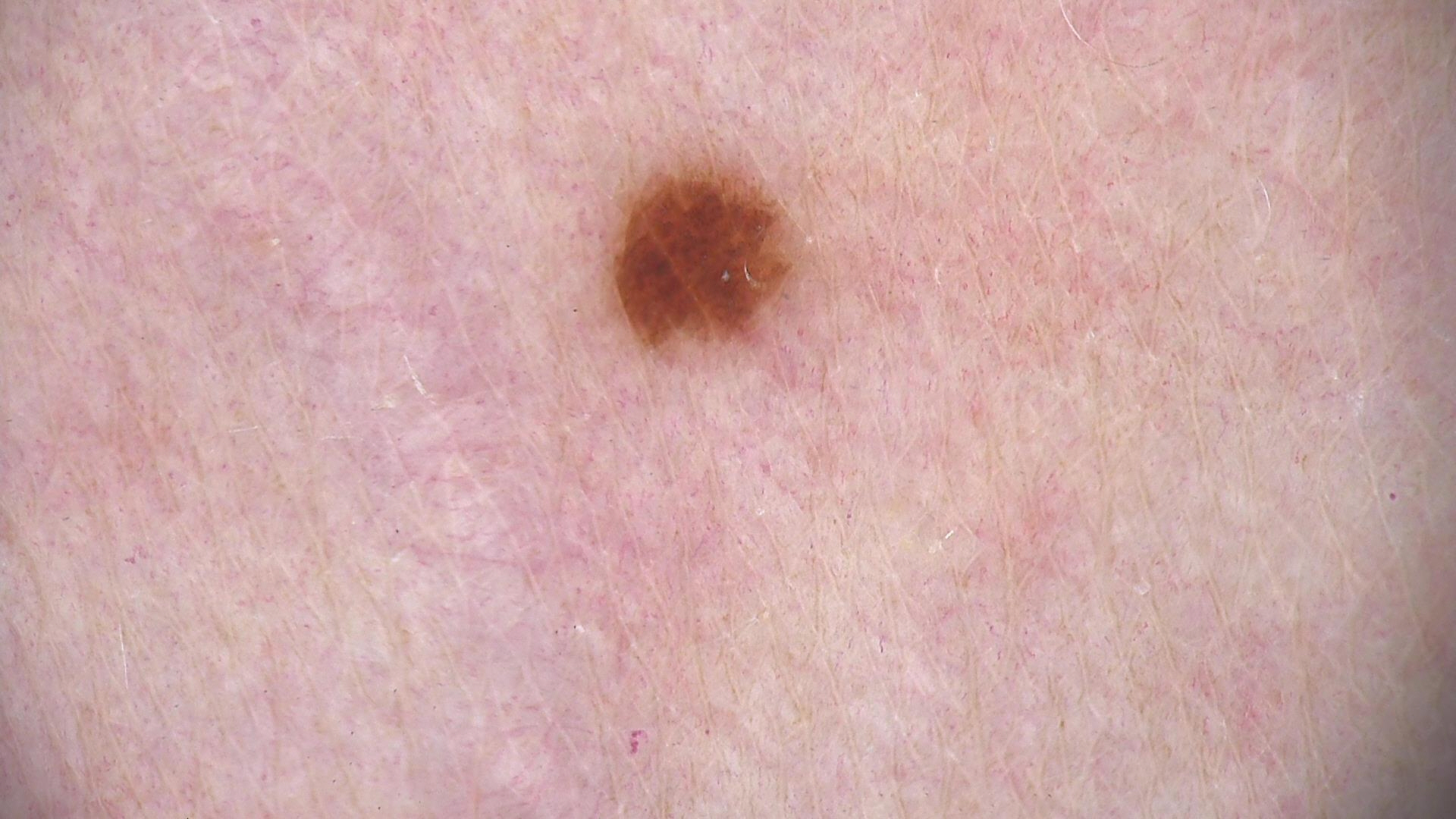image = dermoscopy; class = junctional nevus (expert consensus).